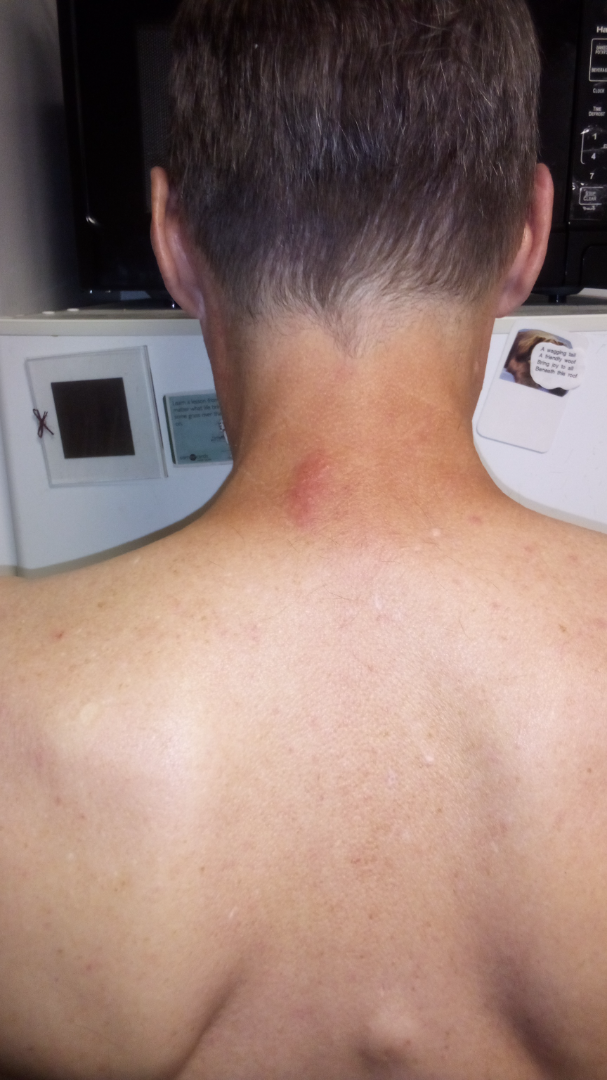The reviewer was unable to grade this case for skin condition.
The affected area is the head or neck.
This image was taken at a distance.